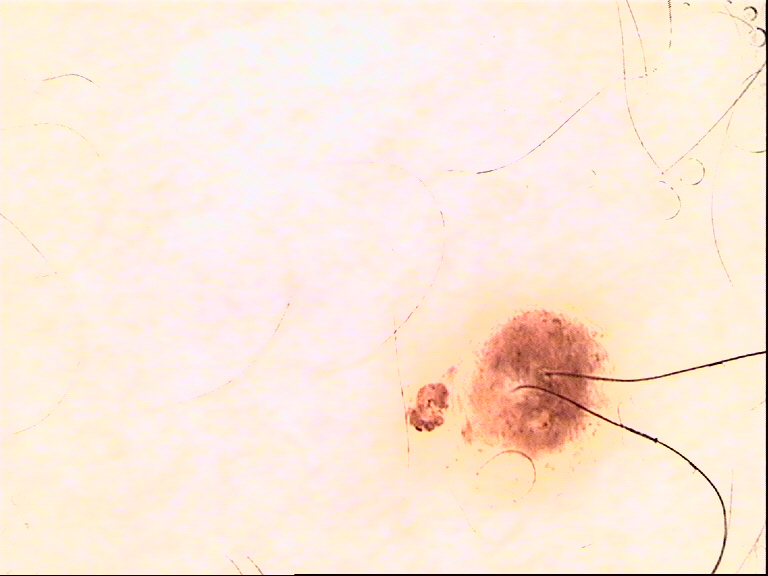  image: dermoscopy
  lesion_type:
    main_class: banal
    pattern: compound
  diagnosis:
    name: compound nevus
    code: cb
    malignancy: benign
    super_class: melanocytic
    confirmation: expert consensus